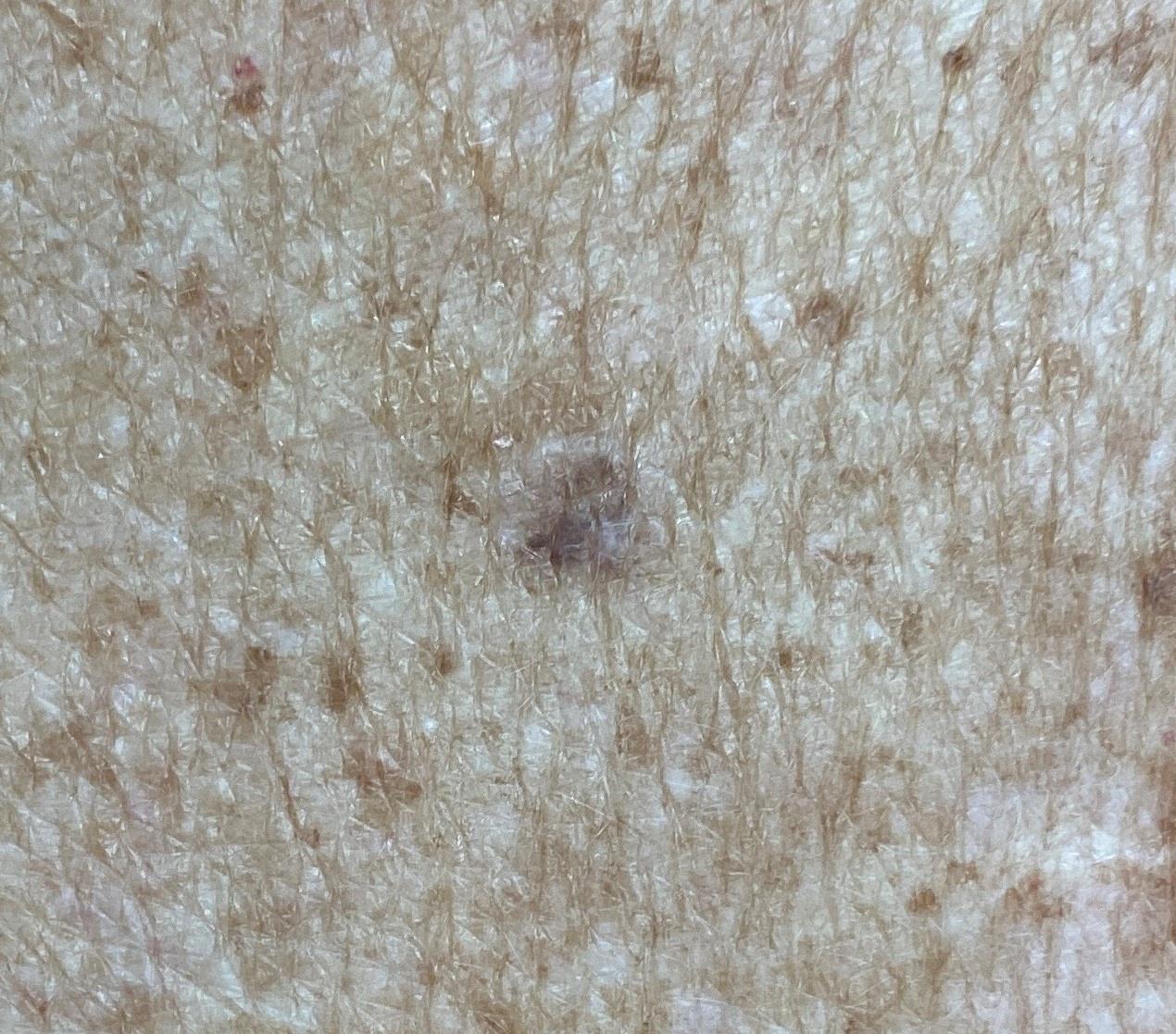Clinical context:
A clinical overview photograph of a skin lesion. Recorded as Fitzpatrick skin type II. A female subject aged around 60. The lesion is on the trunk, specifically the posterior trunk.
Conclusion:
Biopsy-confirmed as a lesion of melanocytic lineage — a nevus.